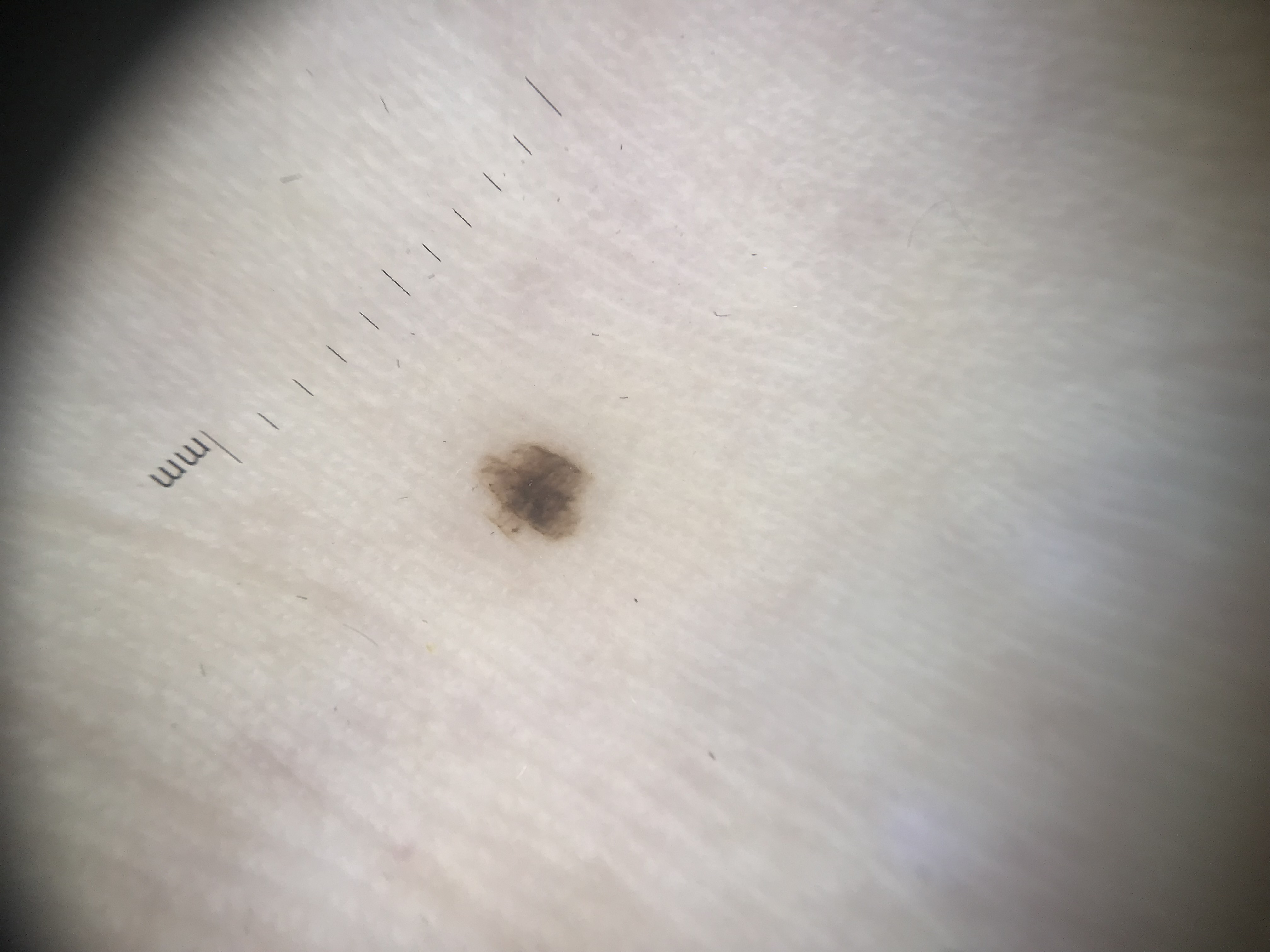modality = dermoscopy | diagnosis = acral dysplastic junctional nevus (expert consensus).